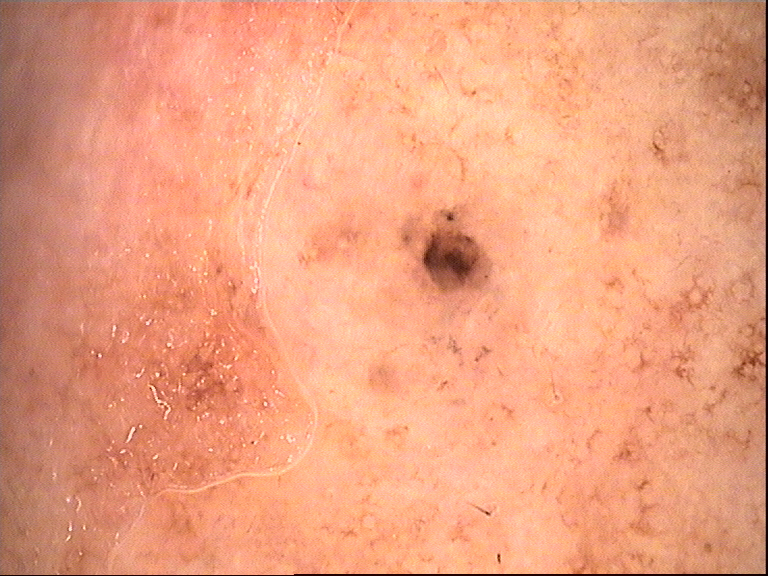Diagnosis: Histopathologically confirmed as a basal cell carcinoma.